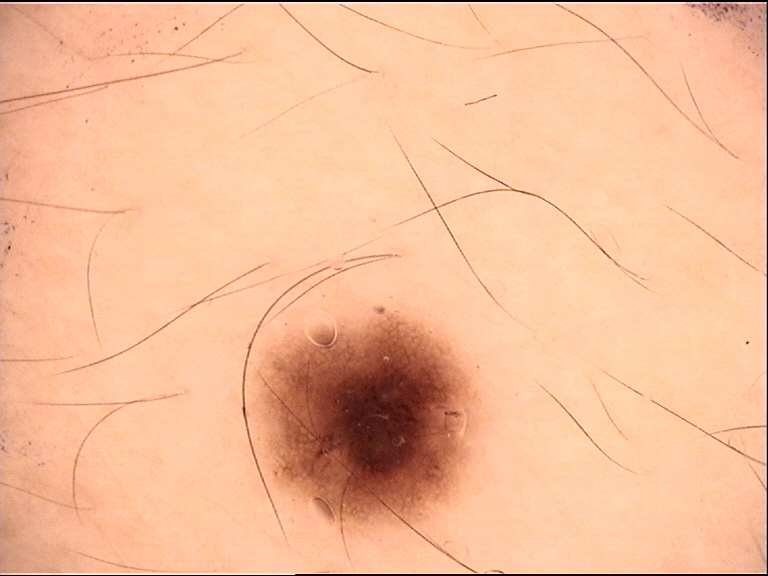| field | value |
|---|---|
| diagnosis | junctional nevus (expert consensus) |